A dermoscopic close-up of a skin lesion. A female patient aged 38 to 42: 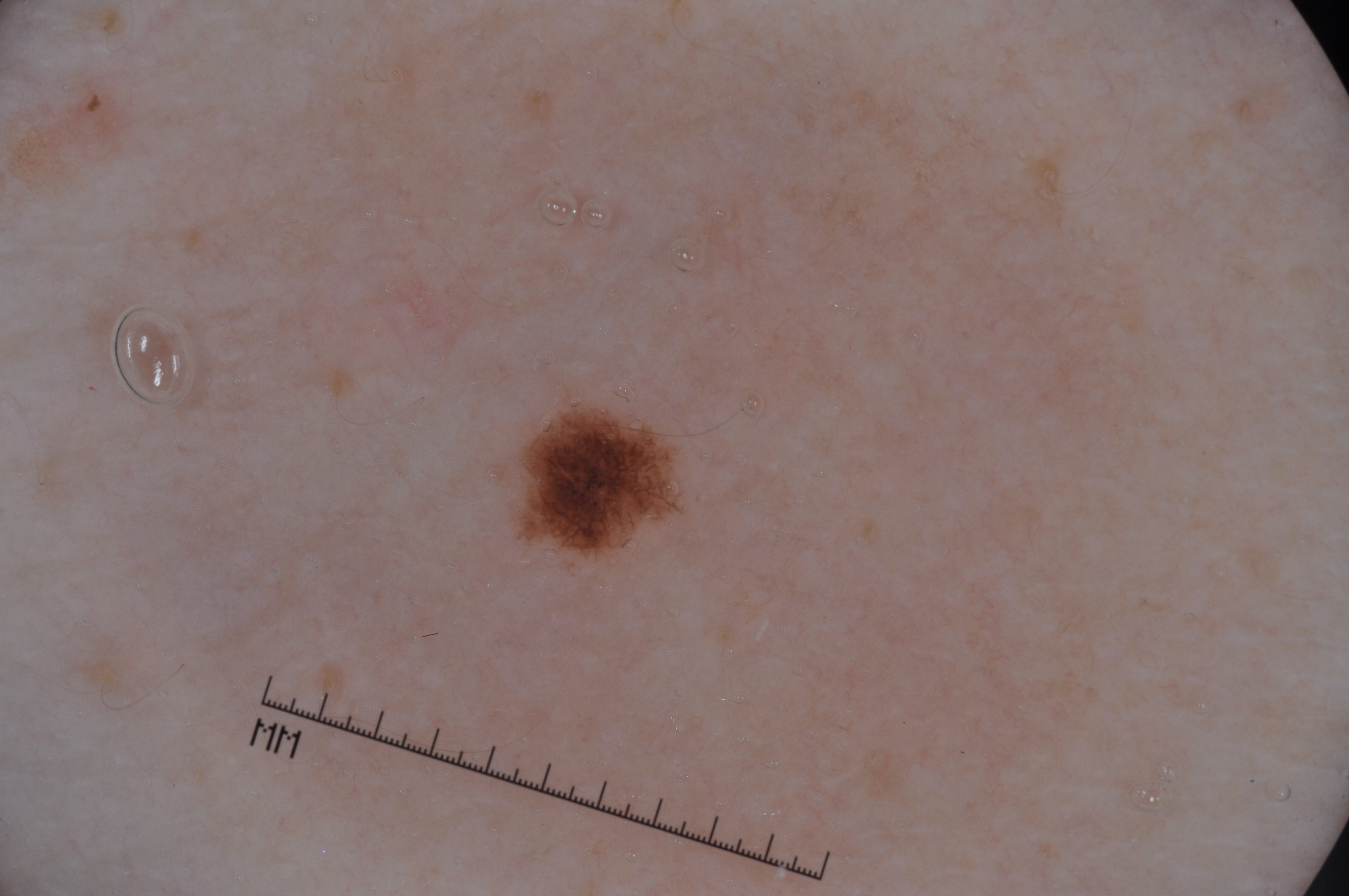* dermoscopic pattern · pigment network
* lesion location · <bbox>506, 406, 685, 560</bbox>
* lesion size · small
* diagnostic label · a melanocytic nevus